A skin lesion imaged with a dermatoscope: 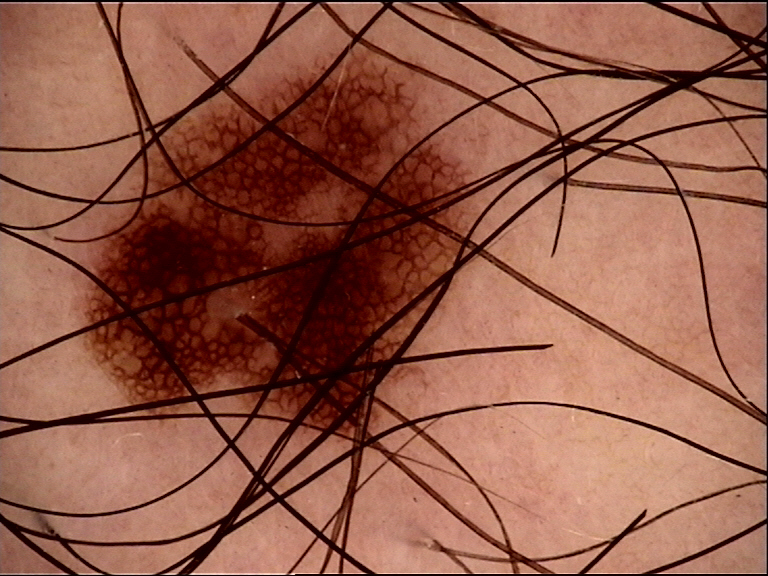Labeled as a dysplastic junctional nevus.